A clinical overview photograph of a skin lesion.
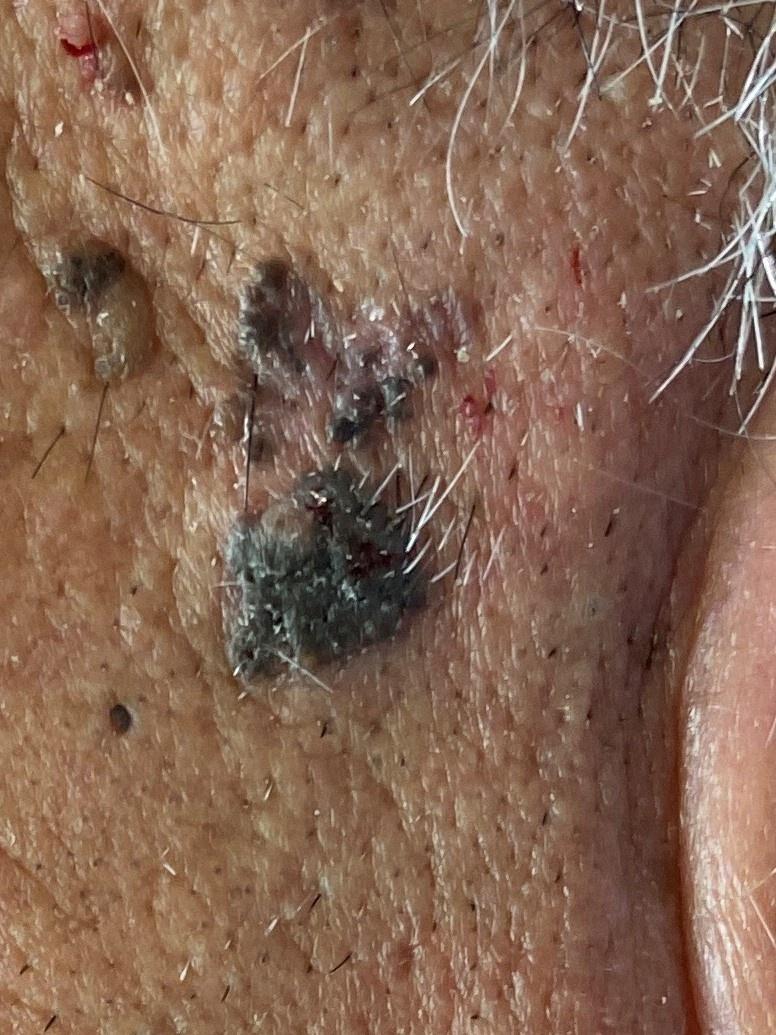Image and clinical context:
Located on the head or neck.
Diagnosis:
Biopsy-confirmed as a basal cell carcinoma.